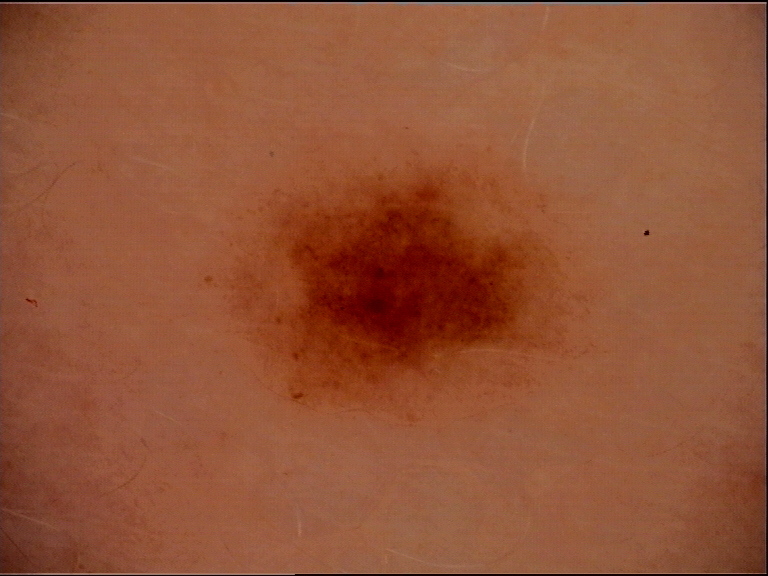<case>
<diagnosis>
<name>junctional nevus</name>
<code>jb</code>
<malignancy>benign</malignancy>
<super_class>melanocytic</super_class>
<confirmation>expert consensus</confirmation>
</diagnosis>
</case>